The photograph is a close-up of the affected area, the lesion involves the arm, self-categorized by the patient as a rash, Fitzpatrick phototype II, the condition has been present for less than one week, the lesion is associated with itching, texture is reported as raised or bumpy: 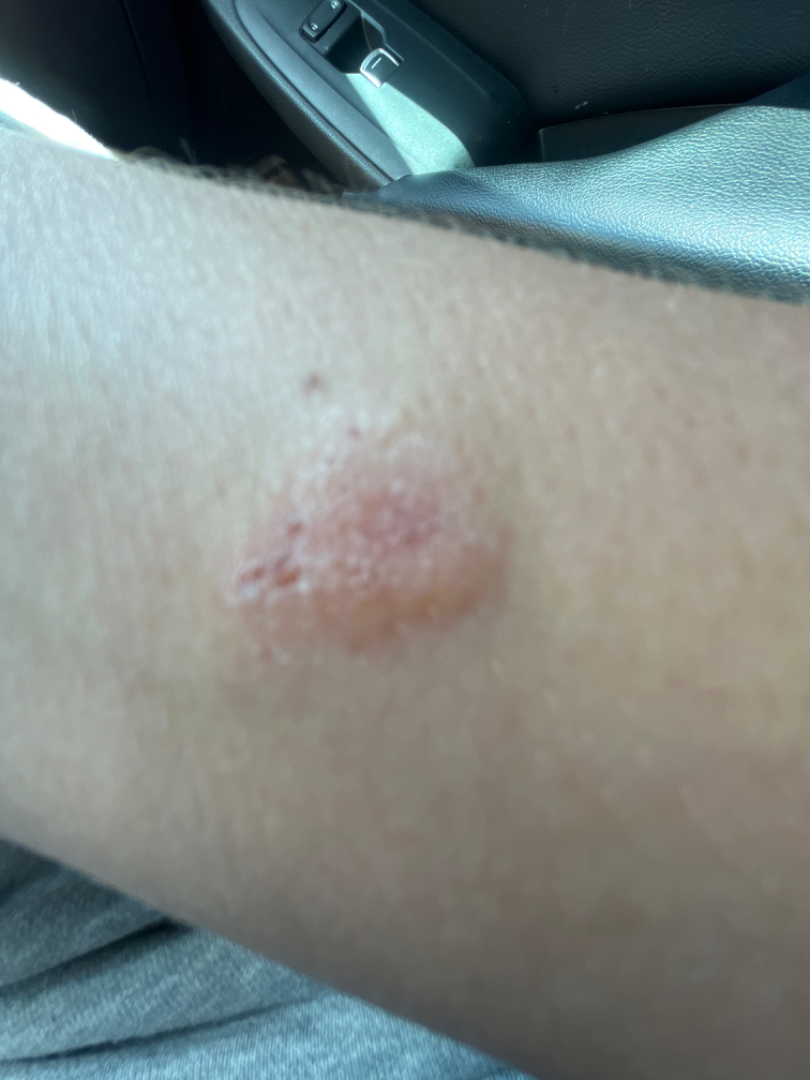The skin findings could not be characterized from the image.